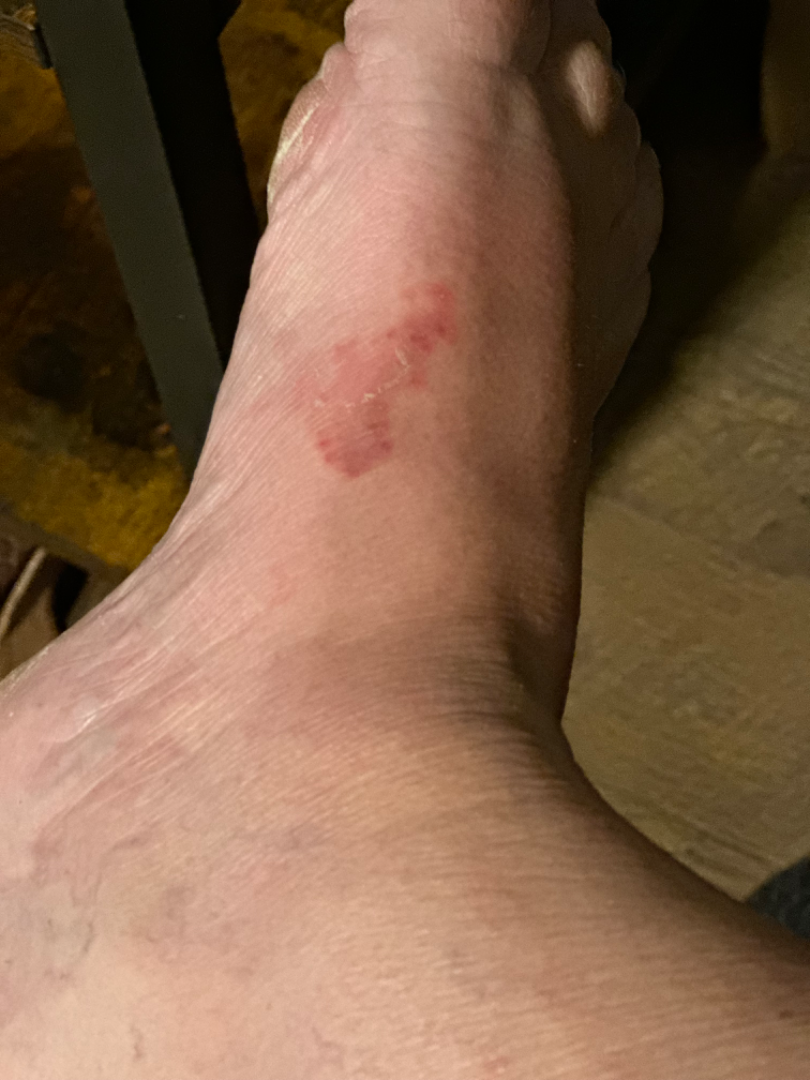<case>
  <differential>
    <leading>Tinea</leading>
    <considered>Psoriasis</considered>
    <unlikely>Eczema</unlikely>
  </differential>
</case>